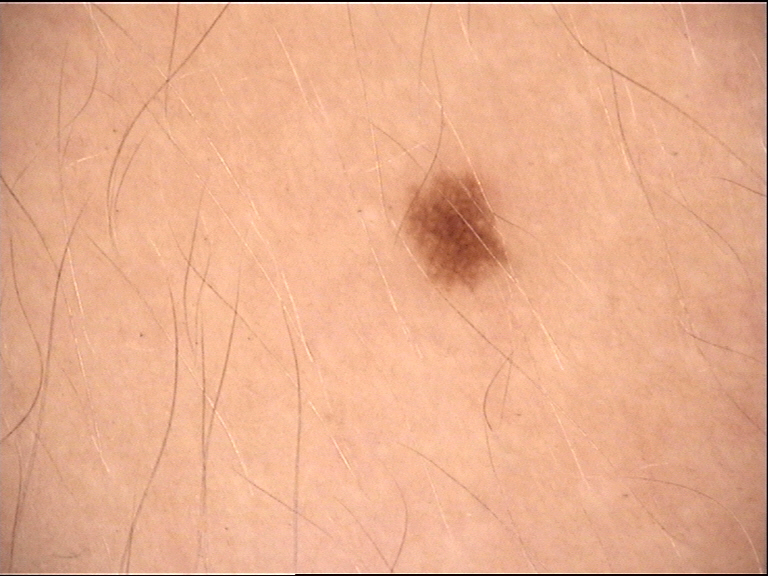A dermoscopic image of a skin lesion. This is a banal lesion. Consistent with a junctional nevus.